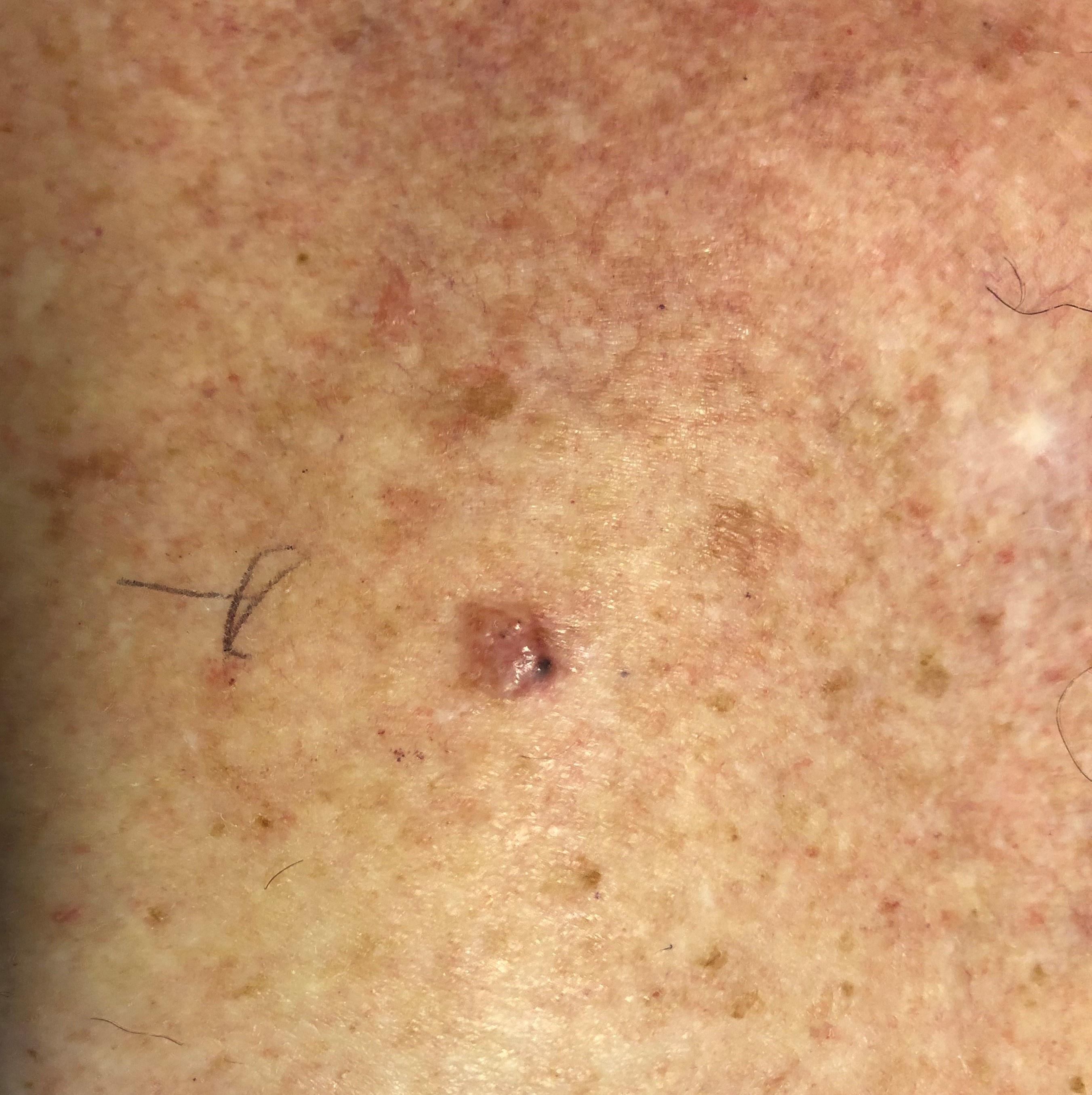Image and clinical context: A male subject aged approximately 85 or older. A clinical overview photograph of a skin lesion. The lesion was found on the trunk. Pathology: Biopsy-confirmed as a basal cell carcinoma.